The arm is involved · the photograph is a close-up of the affected area.
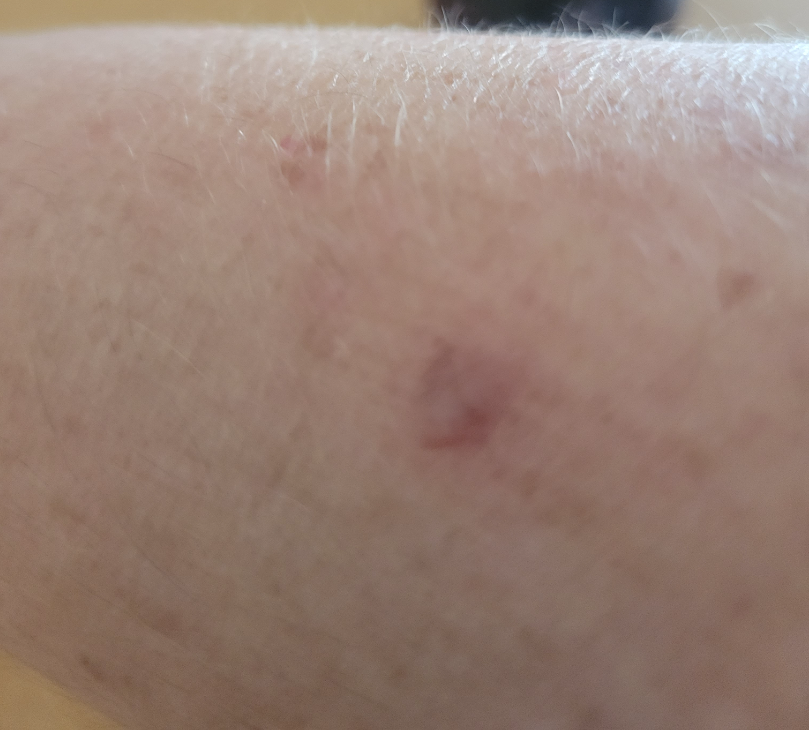assessment: not assessable; history: about one day.